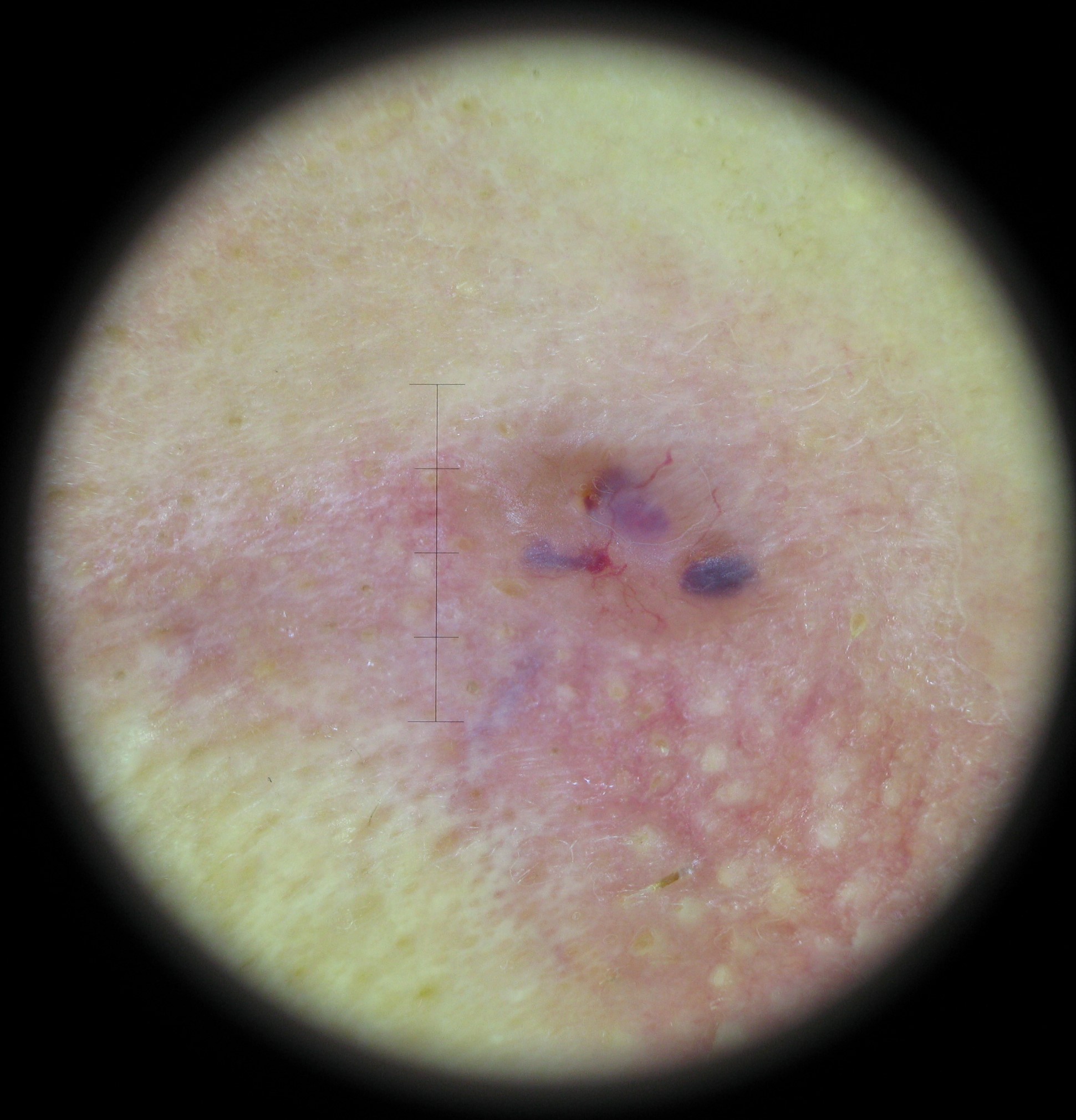Pathology:
The biopsy diagnosis was a basal cell carcinoma.